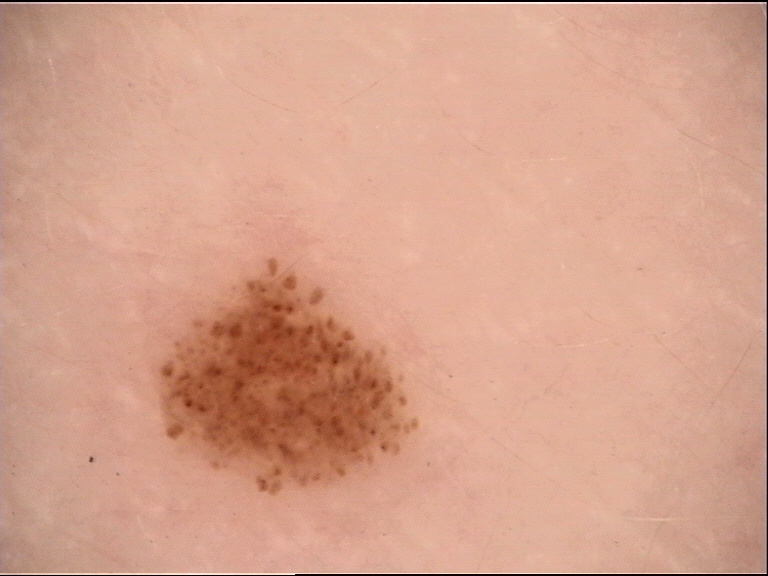Summary:
A skin lesion imaged with a dermatoscope.
Conclusion:
Consistent with a banal lesion — a junctional nevus.